A close-up photograph — 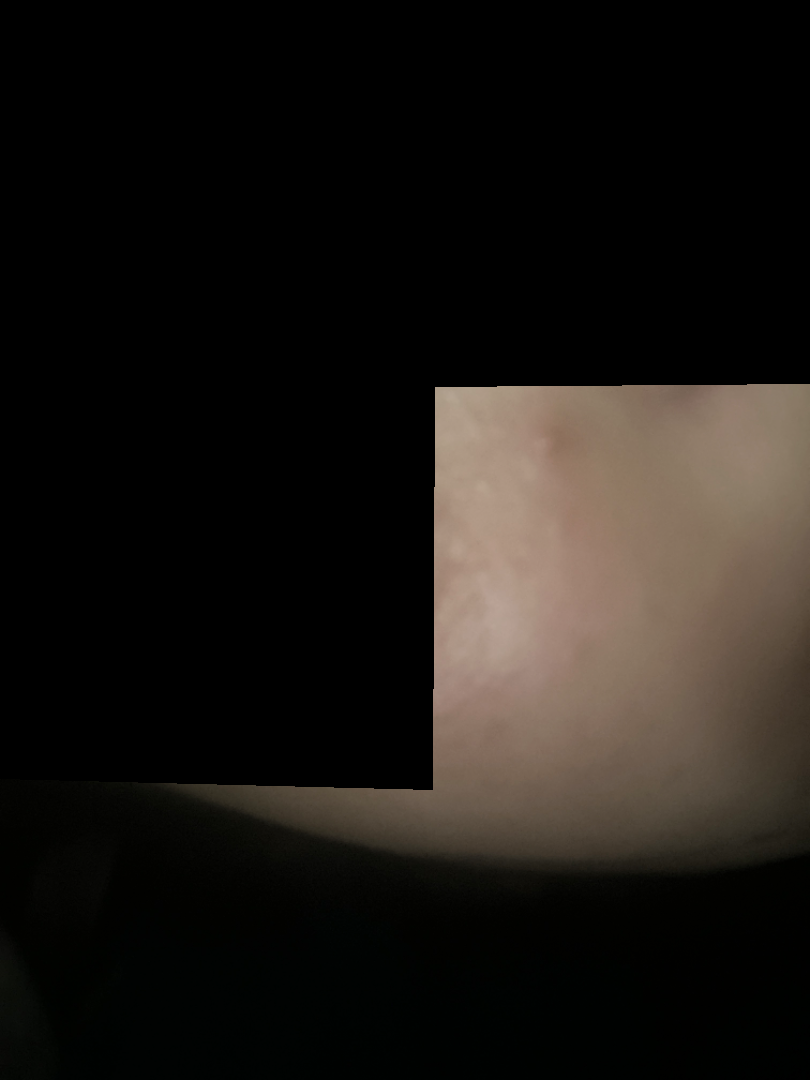The condition could not be reliably identified from the image.